A dermatoscopic image of a skin lesion.
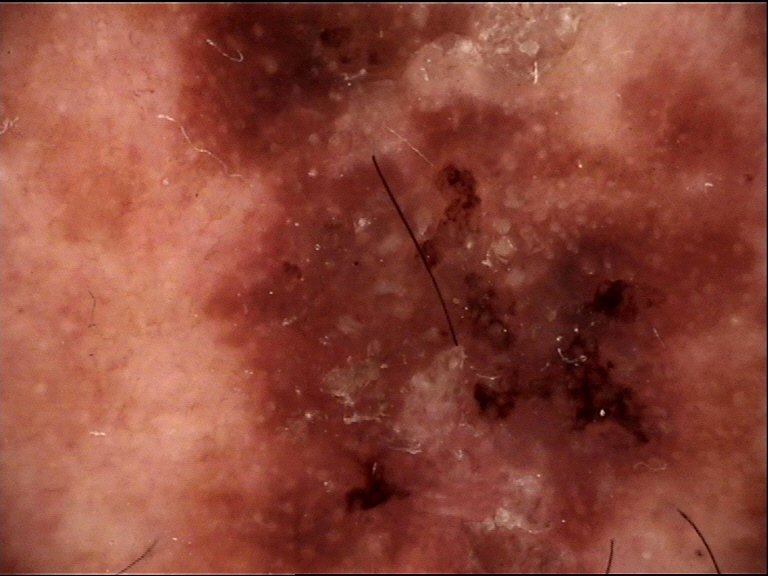{"diagnosis": {"name": "lentigo maligna", "code": "lm", "malignancy": "malignant", "super_class": "melanocytic", "confirmation": "histopathology"}}